The contributor reports the lesion is flat · the photograph is a close-up of the affected area · located on the arm · self-categorized by the patient as skin that appeared healthy to them · no relevant lesion symptoms reported.
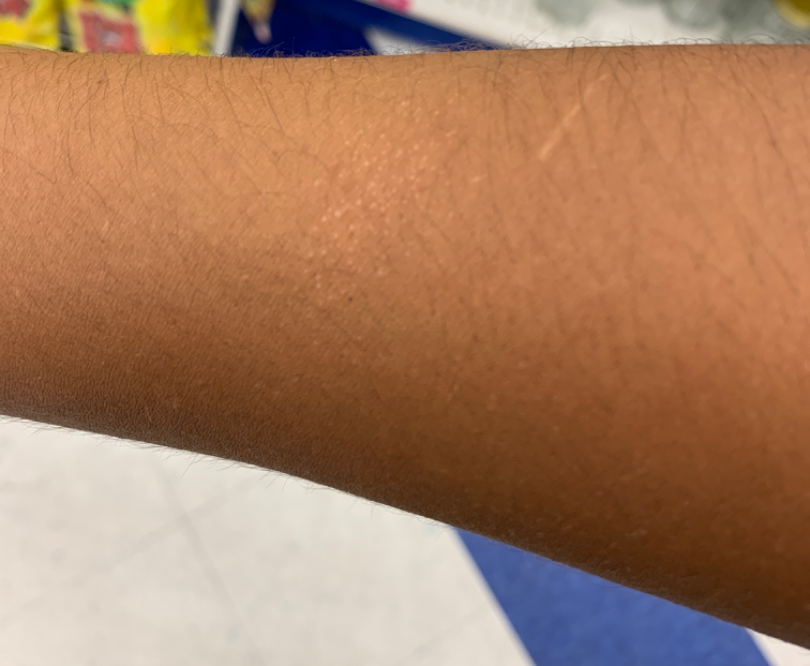The reviewer was unable to grade this case for skin condition.